The affected area is the back of the torso · close-up view · the subject is 30–39, female:
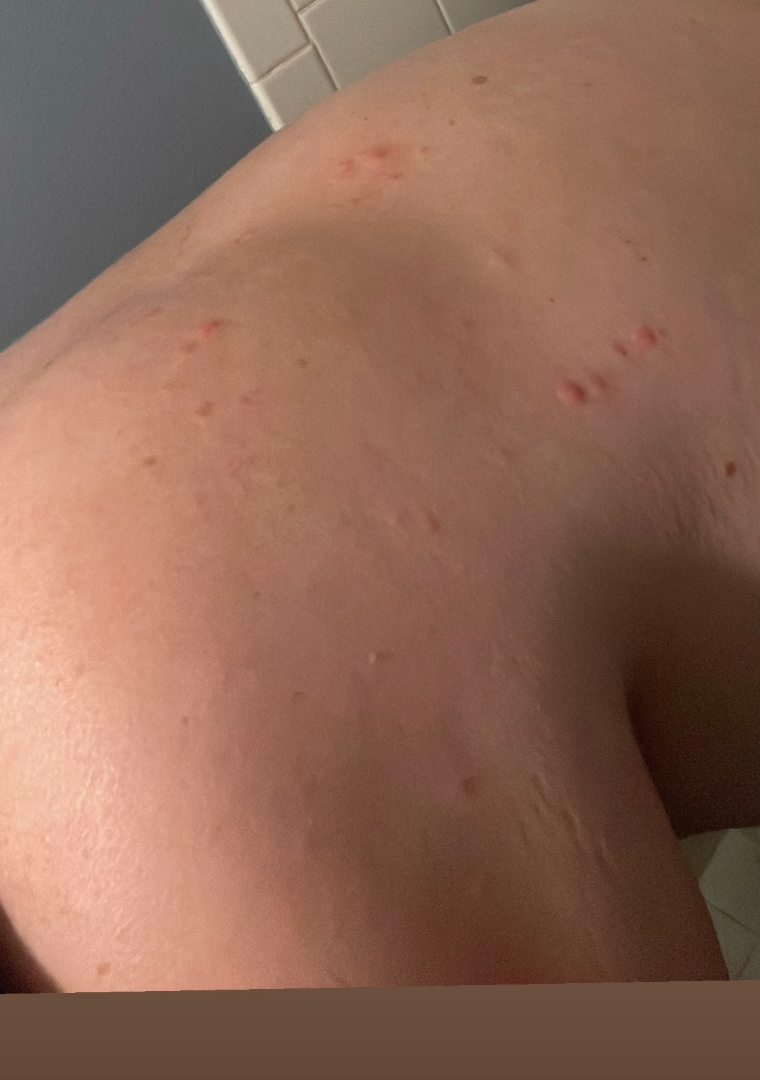assessment: indeterminate
described texture: raised or bumpy
patient describes the issue as: a rash
present for: about one day